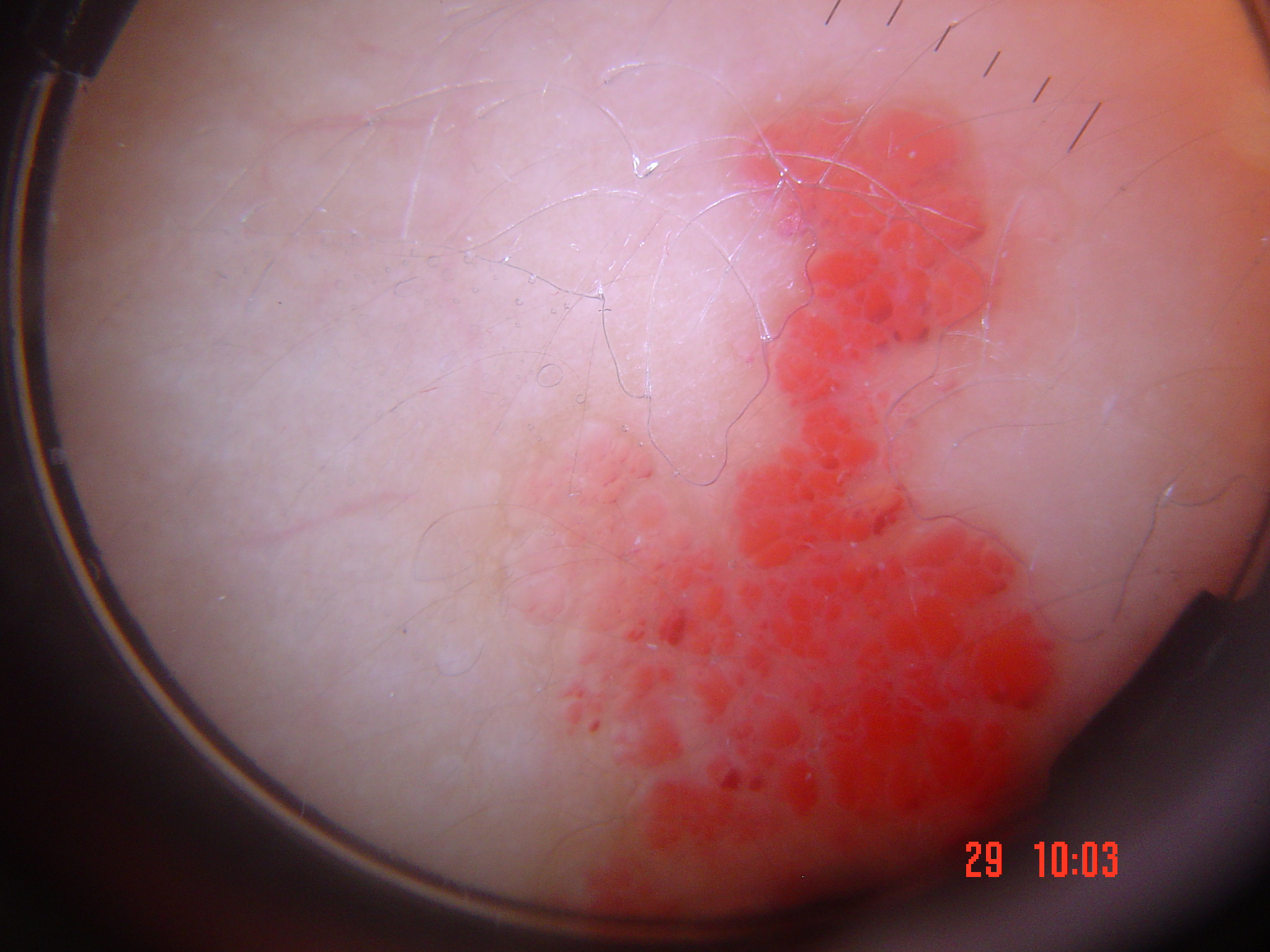A dermatoscopic image of a skin lesion. The diagnosis was a benign, vascular lesion — a lymphangioma.